The photograph is a close-up of the affected area · the lesion involves the leg:
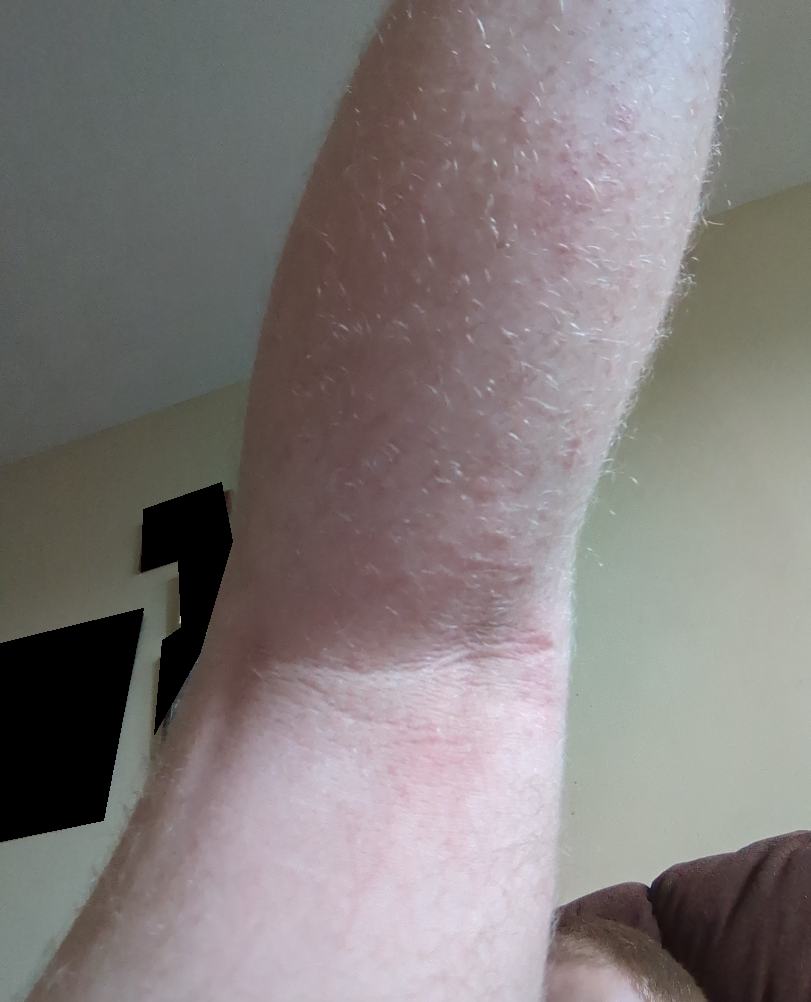Notes:
• assessment — indeterminate from the photograph